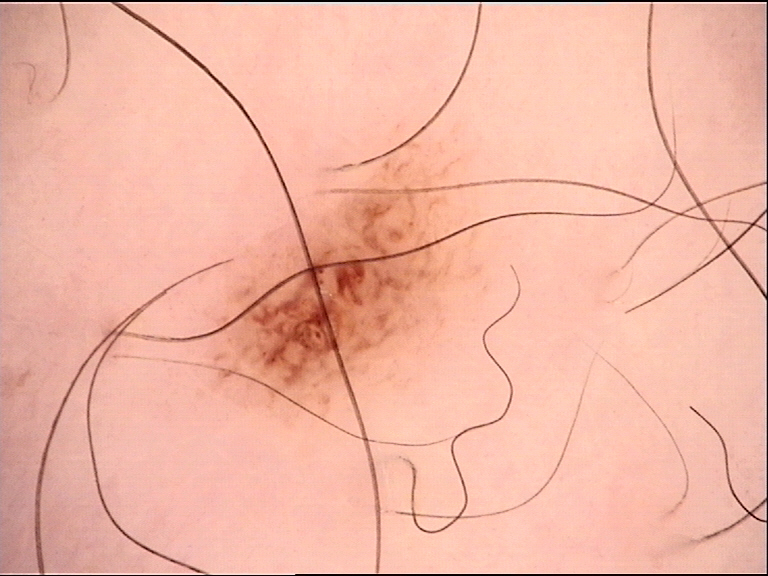Consistent with a benign lesion — a dysplastic junctional nevus.